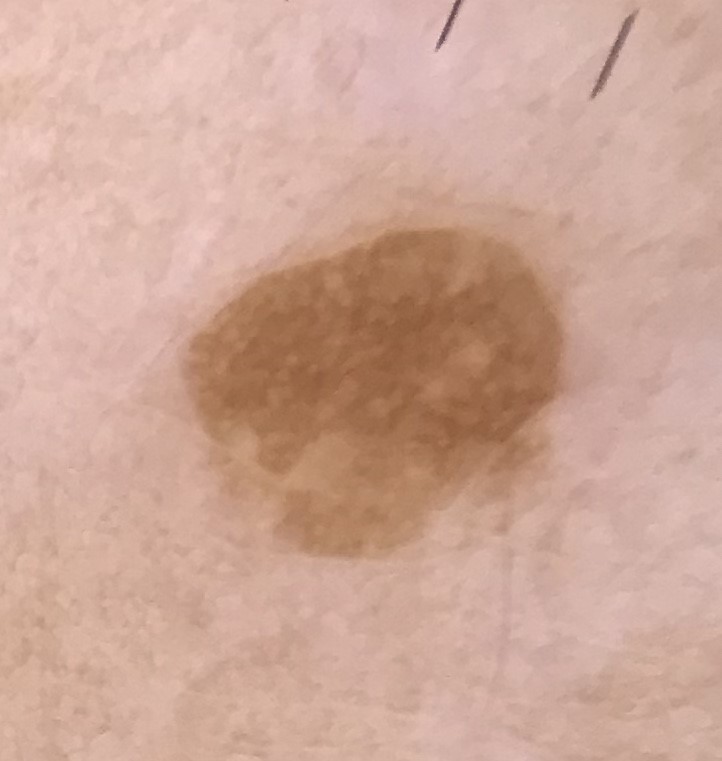label=seborrheic keratosis (expert consensus).